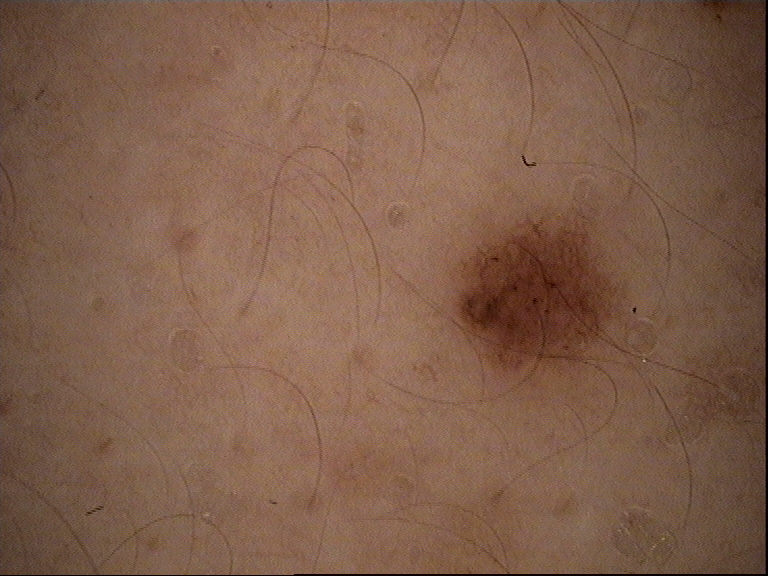The diagnosis was a dysplastic junctional nevus.